A clinical photo of a skin lesion taken with a smartphone; the chart notes prior malignancy (patient or family), pesticide exposure, and no alcohol use; a male subject in their mid-60s; recorded as skin type II.
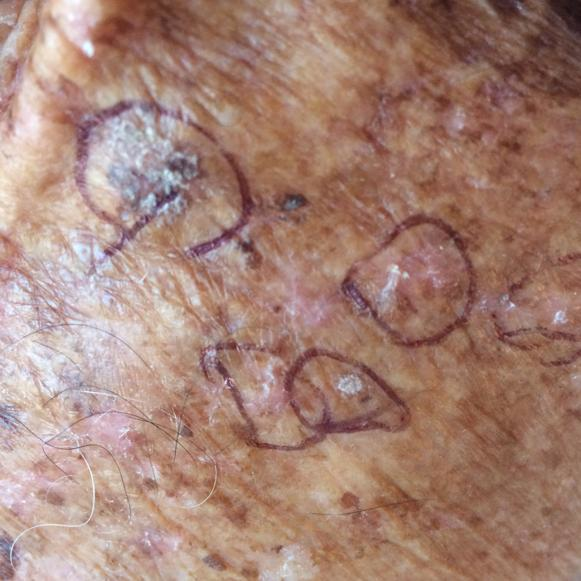The lesion is located on the chest. Measuring about 35 × 15 mm. Per patient report, the lesion has bled and itches, but has not changed and has not grown. Clinically diagnosed as an actinic keratosis.